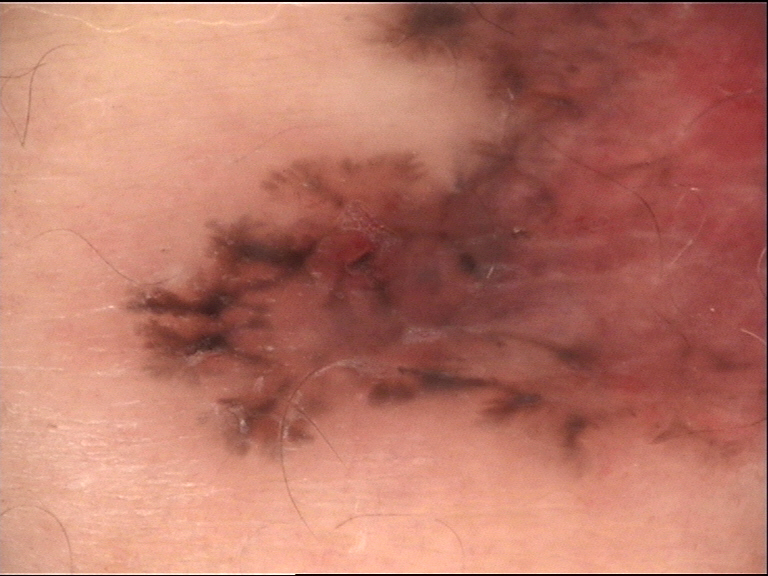Findings:
Dermoscopy of a skin lesion.
Diagnosis:
Confirmed on histopathology as a basal cell carcinoma.